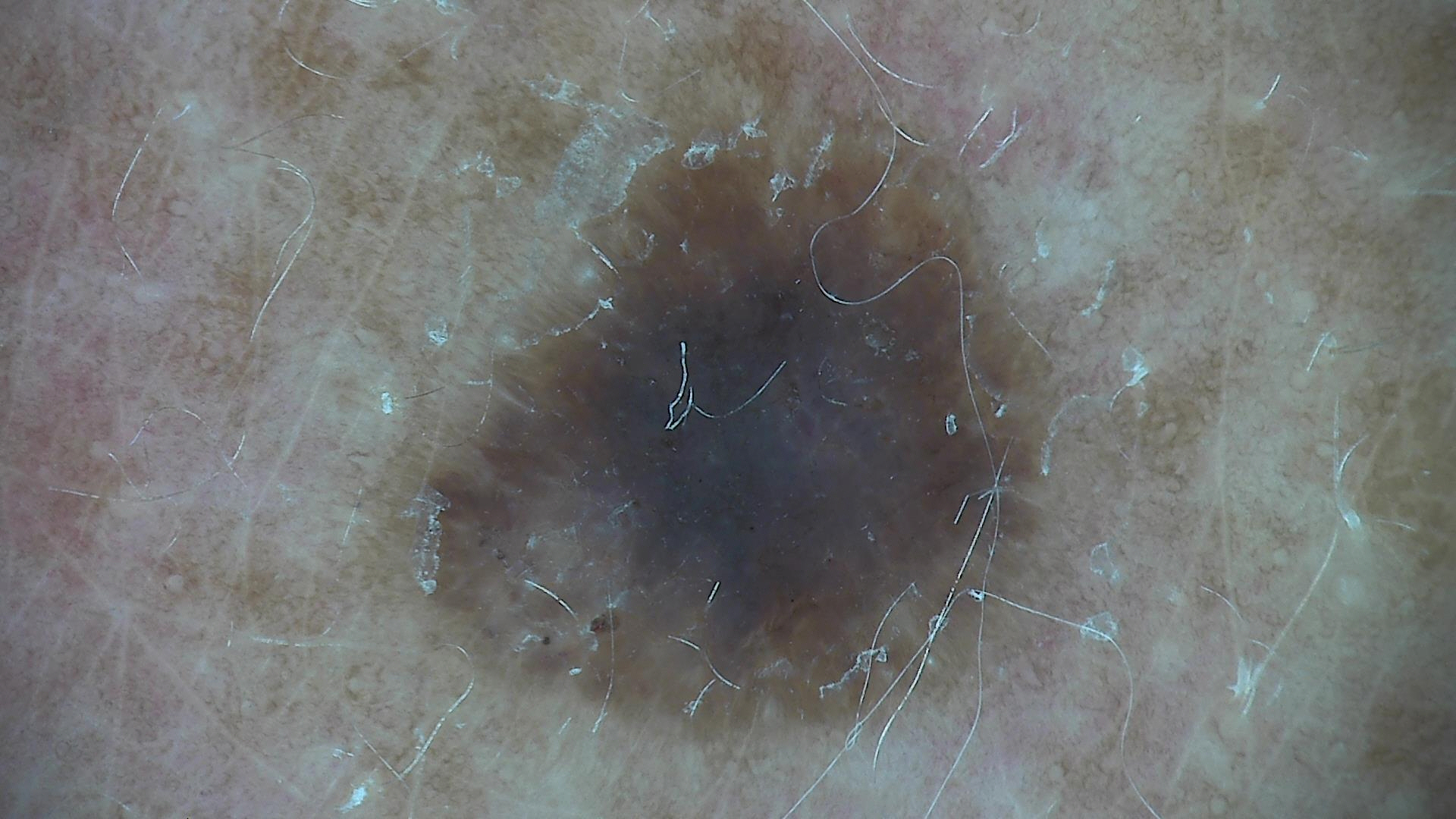Conclusion:
Classified as a seborrheic keratosis.